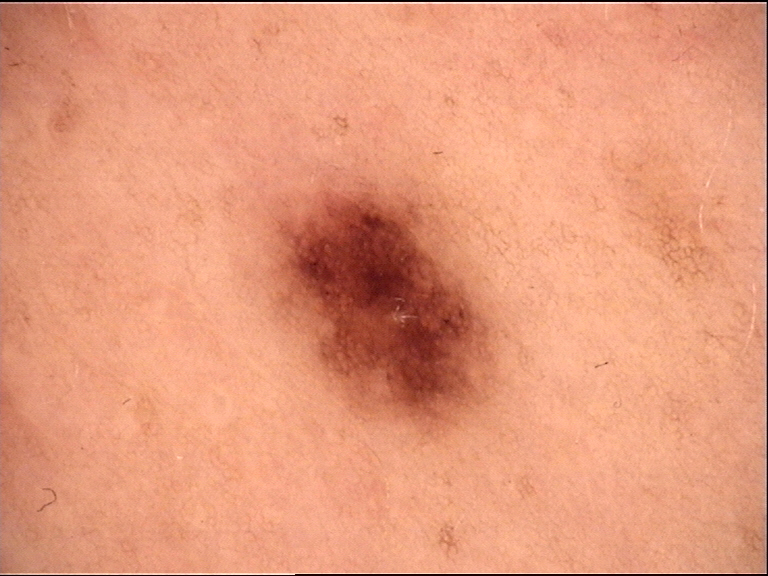A skin lesion imaged with a dermatoscope. The diagnosis was a benign lesion — a dysplastic junctional nevus.